A dermoscopy image of a single skin lesion · a female subject in their 50s: 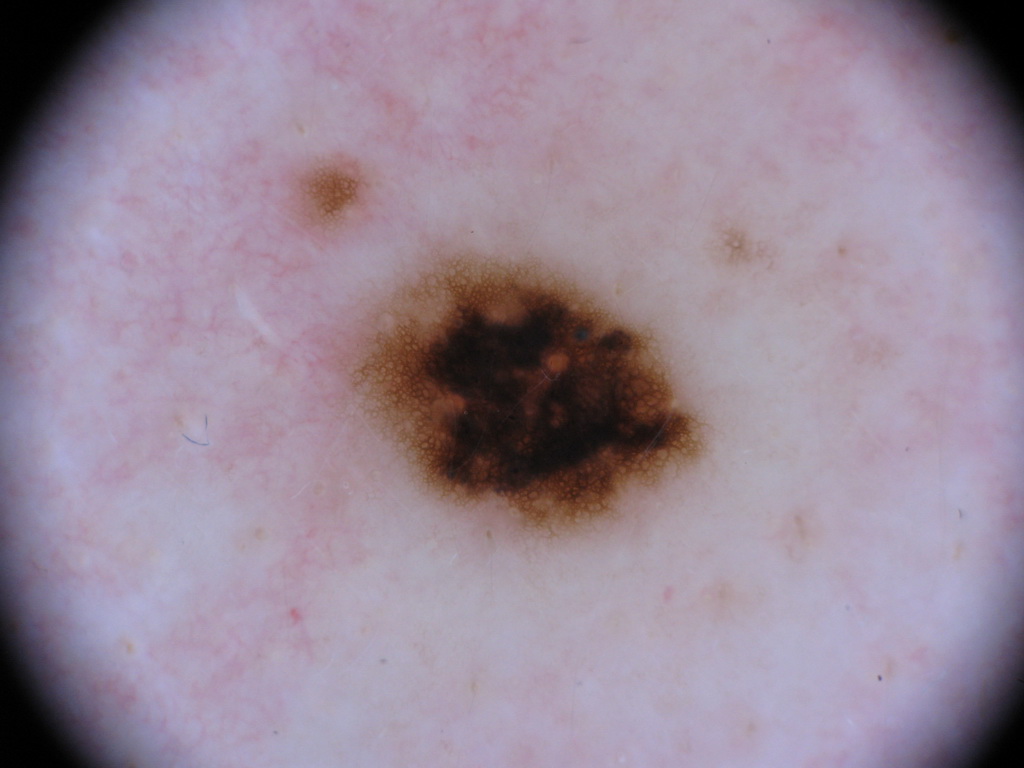Q: What does dermoscopy show?
A: pigment network
Q: Lesion extent?
A: moderate
Q: Where is the lesion in the image?
A: 334/245/723/547
Q: What did the assessment conclude?
A: a melanocytic nevus, a benign skin lesion